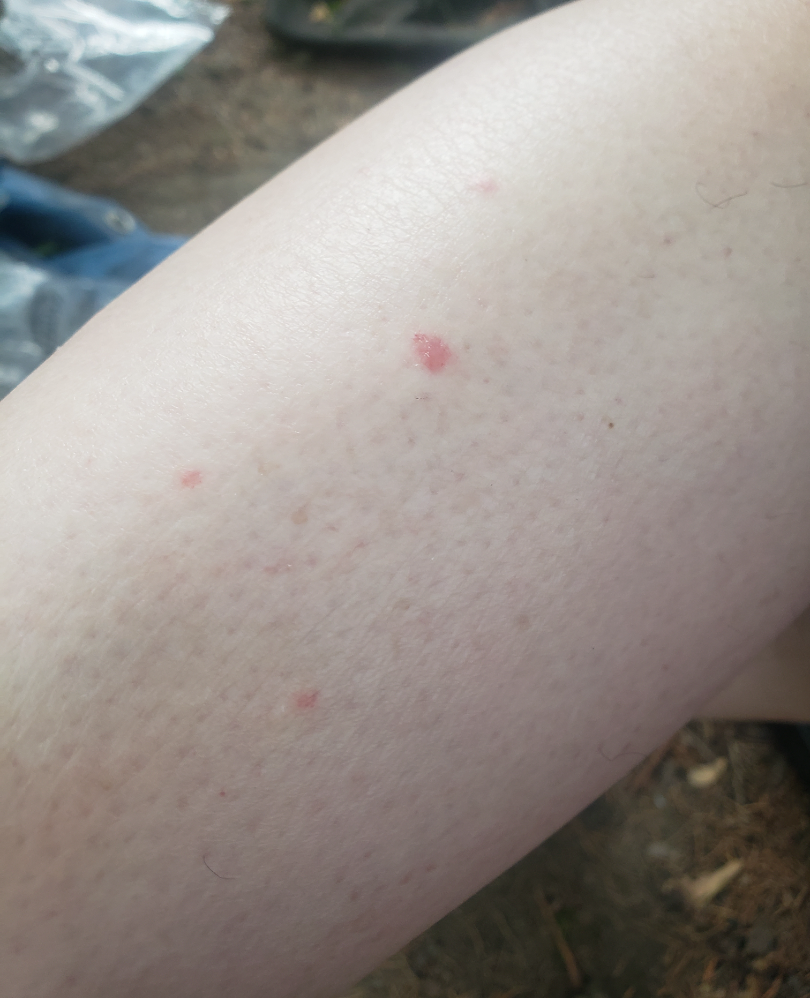differential:
  leading:
    - Eczema
  considered:
    - Psoriasis
  unlikely:
    - Insect Bite